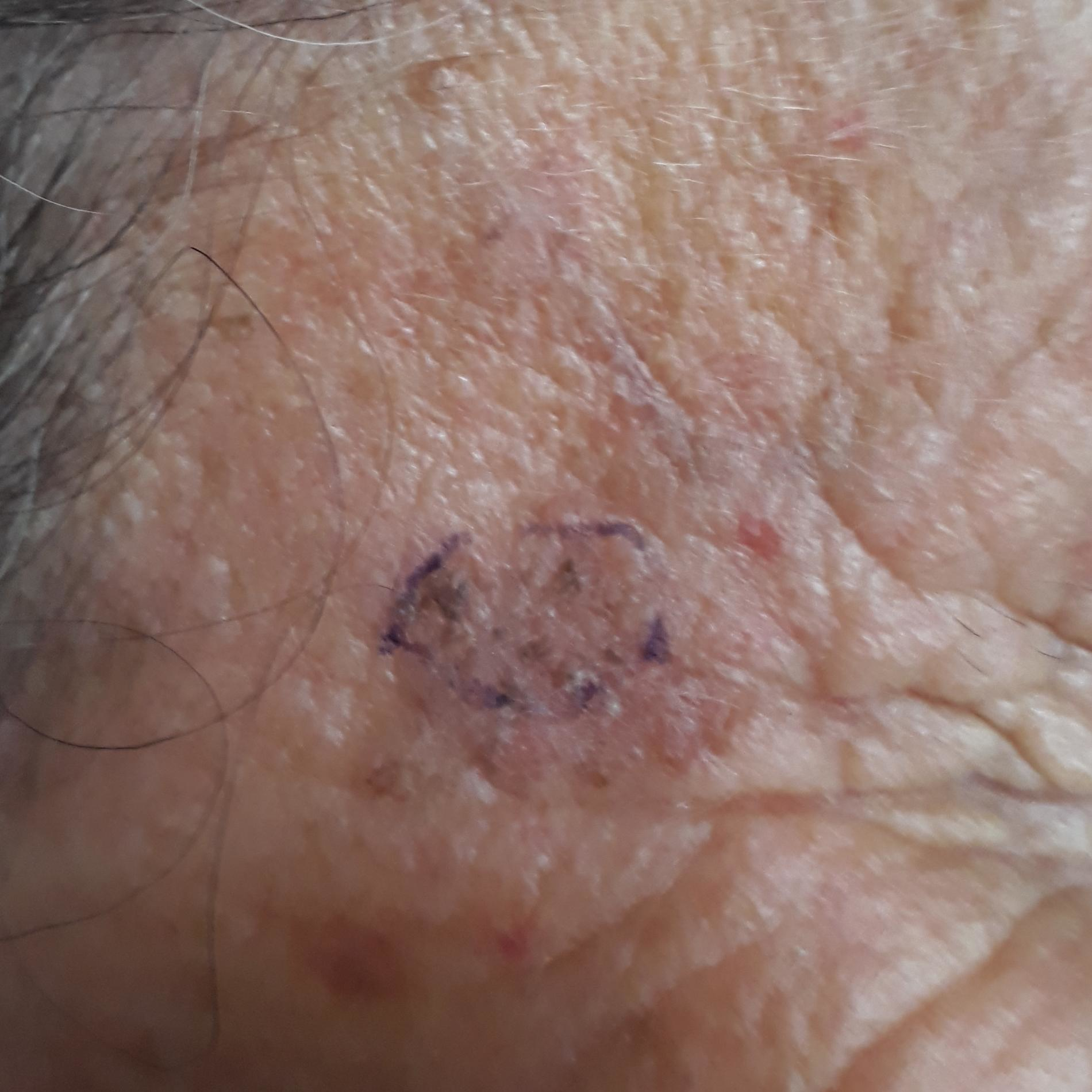Clinical context:
History notes prior malignancy (patient or family), prior skin cancer (patient or family), pesticide exposure, no alcohol use, and no tobacco use. A smartphone photograph of a skin lesion. The lesion is located on the face. The lesion measures approximately 10 × 10 mm. Per patient report, the lesion itches.
Impression:
Diagnosed by dermatologist consensus as a lesion with uncertain malignant potential — an actinic keratosis.